Close-up view; the affected area is the arm, leg, back of the torso, back of the hand and front of the torso; the subject is 18–29, female:
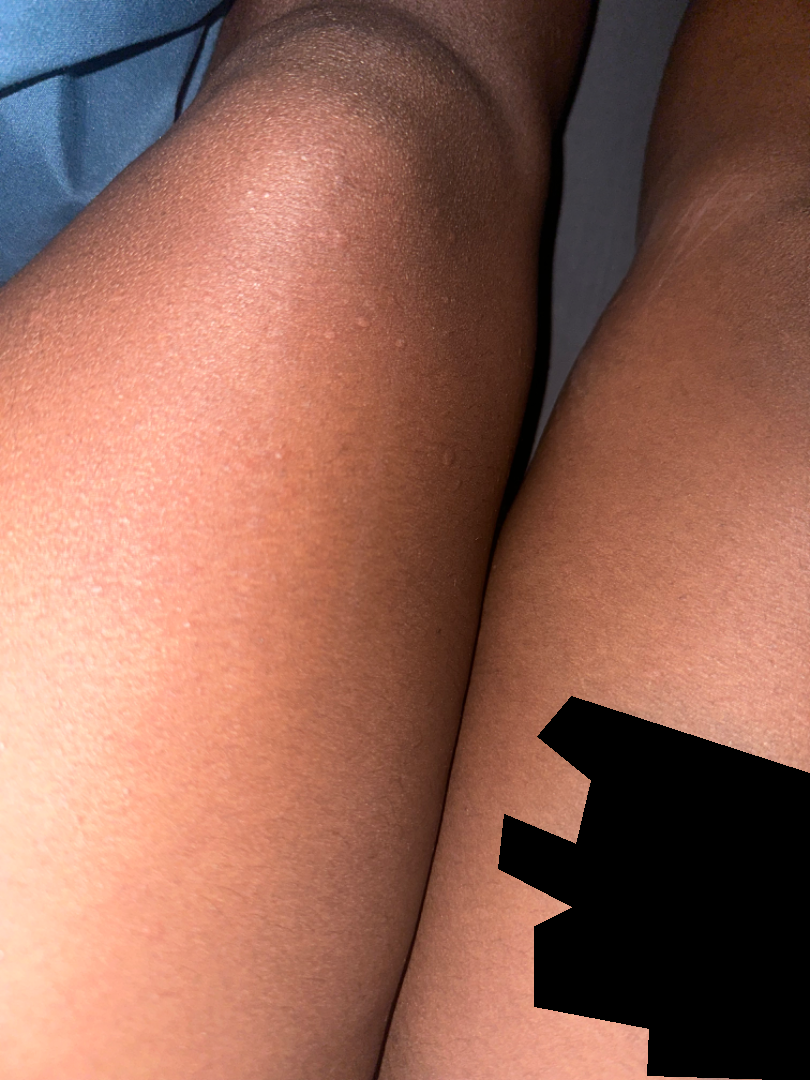assessment: Eczema (leading); Lichen nitidus (possible).